A skin lesion imaged with a dermatoscope.
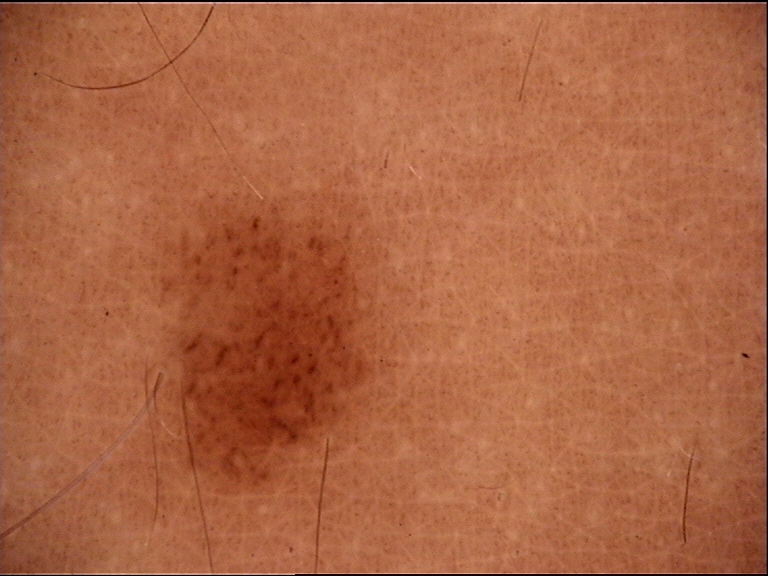Diagnosed as a benign lesion — a dysplastic junctional nevus.